A dermoscopic image of a skin lesion — 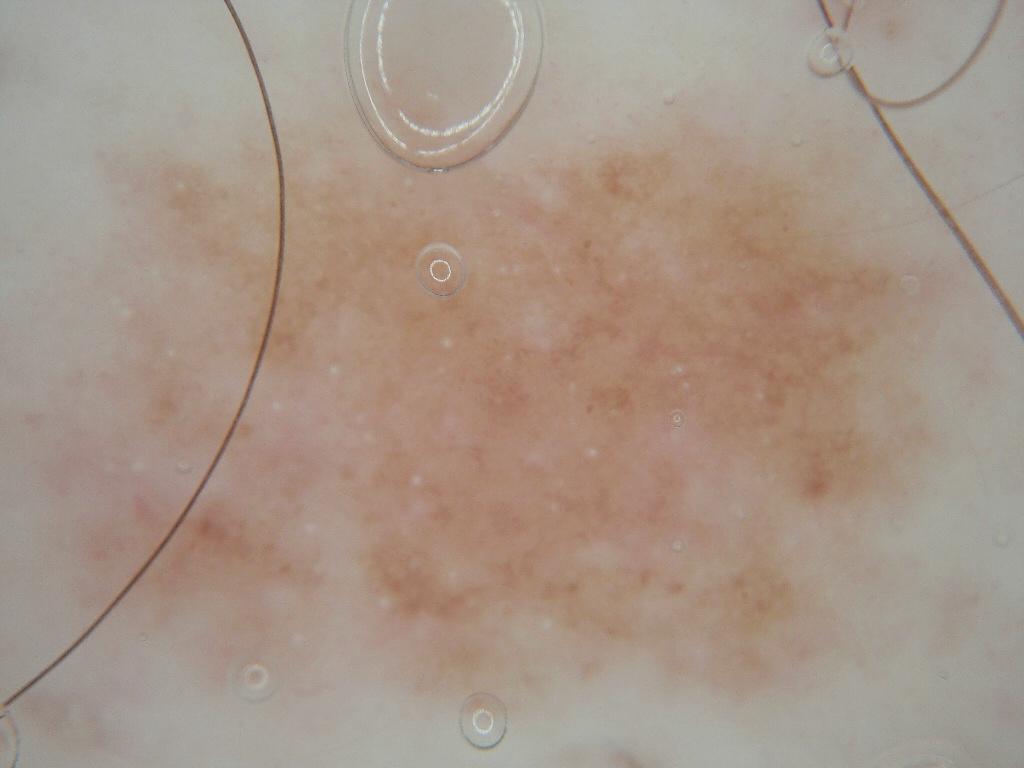extent: ~72% of the field; lesion bbox: 4, 90, 991, 748; impression: a benign skin lesion.